A dermoscopy image of a single skin lesion; the patient is a male approximately 30 years of age — 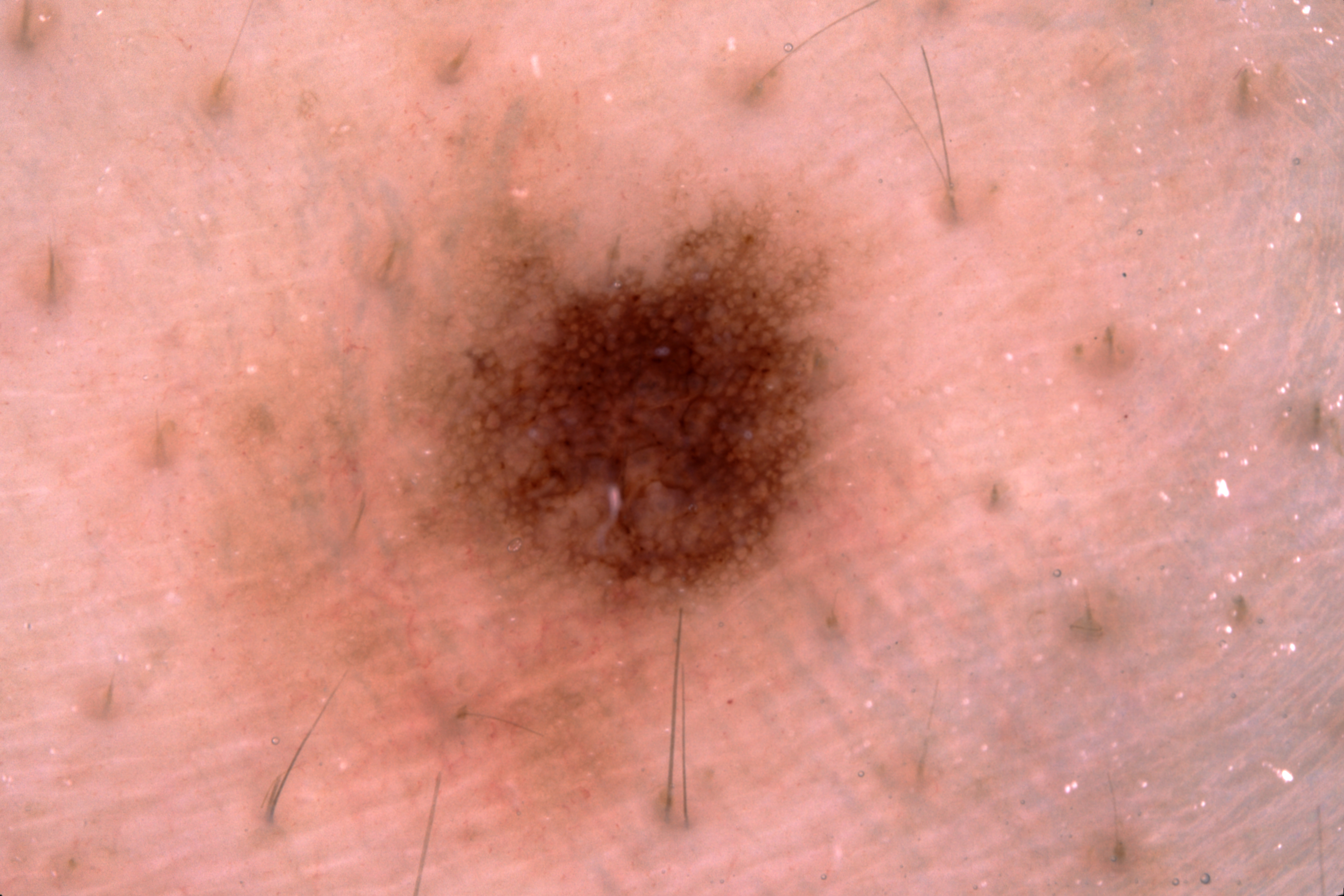Q: Where is the lesion located?
A: <box>221, 196, 861, 819</box>
Q: What does dermoscopy show?
A: milia-like cysts and pigment network
Q: What is the diagnosis?
A: a melanocytic nevus